The patient notes burning, enlargement and itching; the photograph was taken at a distance; lay reviewers estimated Monk skin tone scale 3 or 4; located on the arm and head or neck; self-categorized by the patient as skin that appeared healthy to them; the patient notes the condition has been present for more than five years — 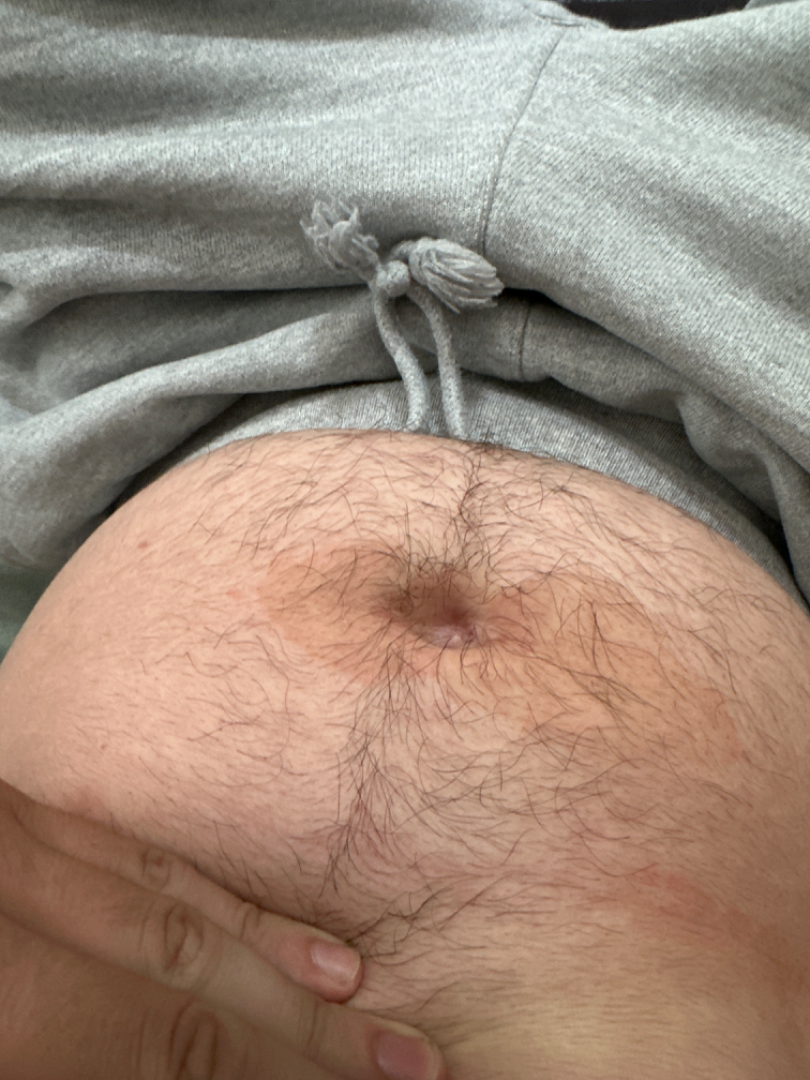The skin condition could not be confidently assessed from this image.